The patient is a male in their mid-40s. A skin lesion imaged with a dermatoscope: 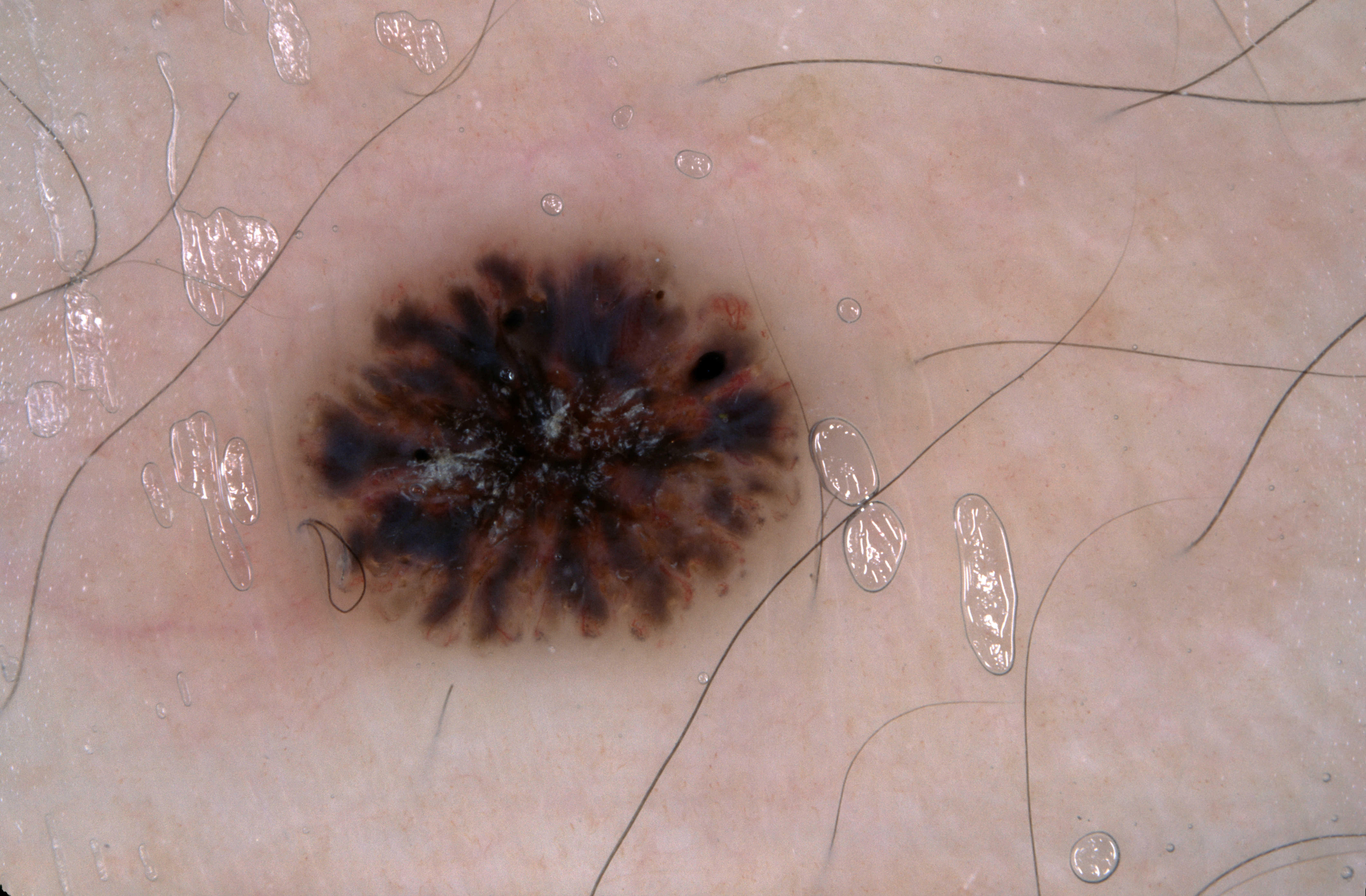The lesion covers approximately 15% of the dermoscopic field. With coordinates (x1, y1, x2, y2), the visible lesion spans <box>278, 231, 811, 658</box>. Dermoscopic examination shows streaks. Diagnosed as a seborrheic keratosis, a keratinocytic lesion.